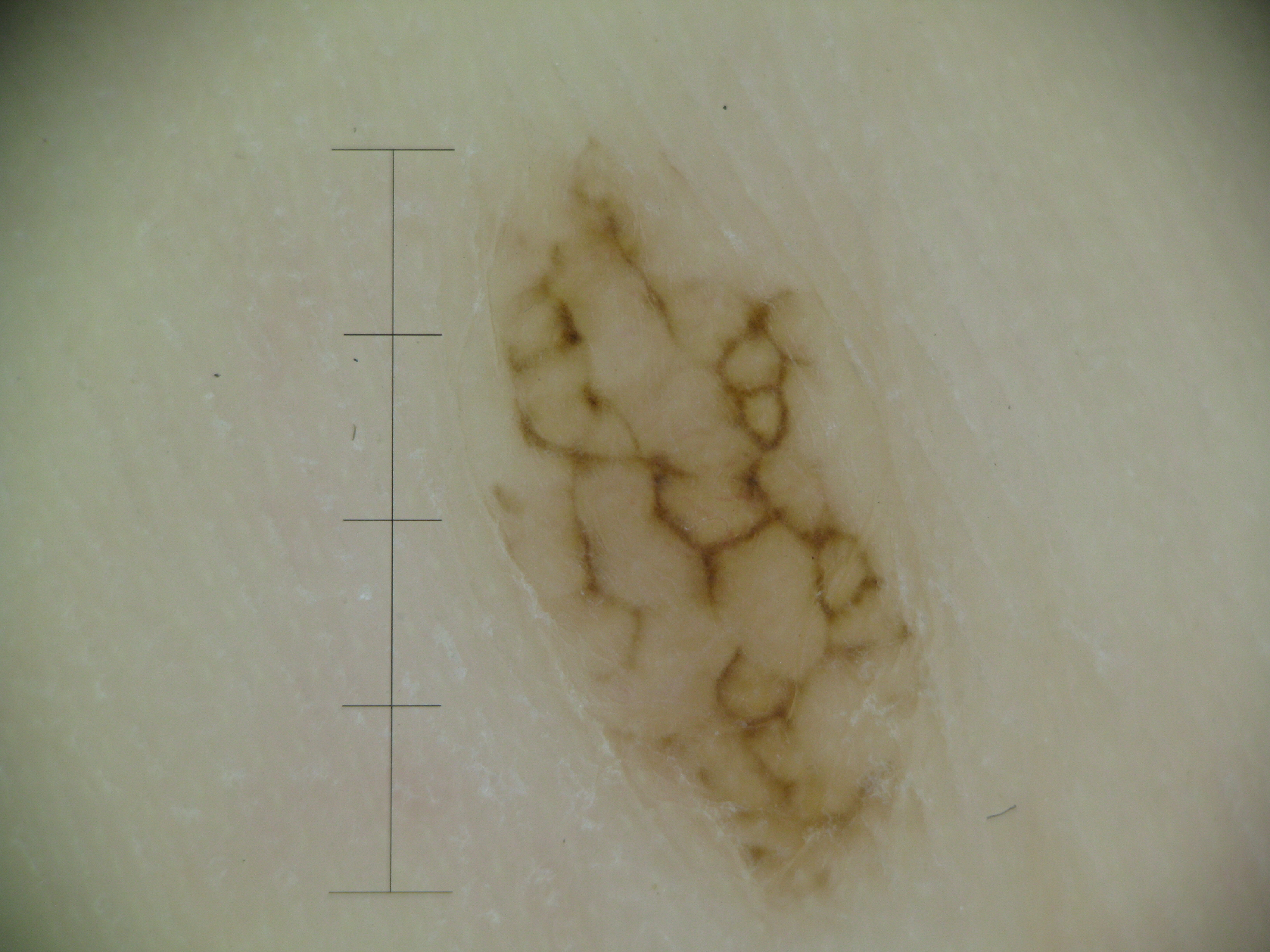The architecture is that of a banal lesion. Labeled as an acral compound nevus.